A dermoscopy image of a single skin lesion: 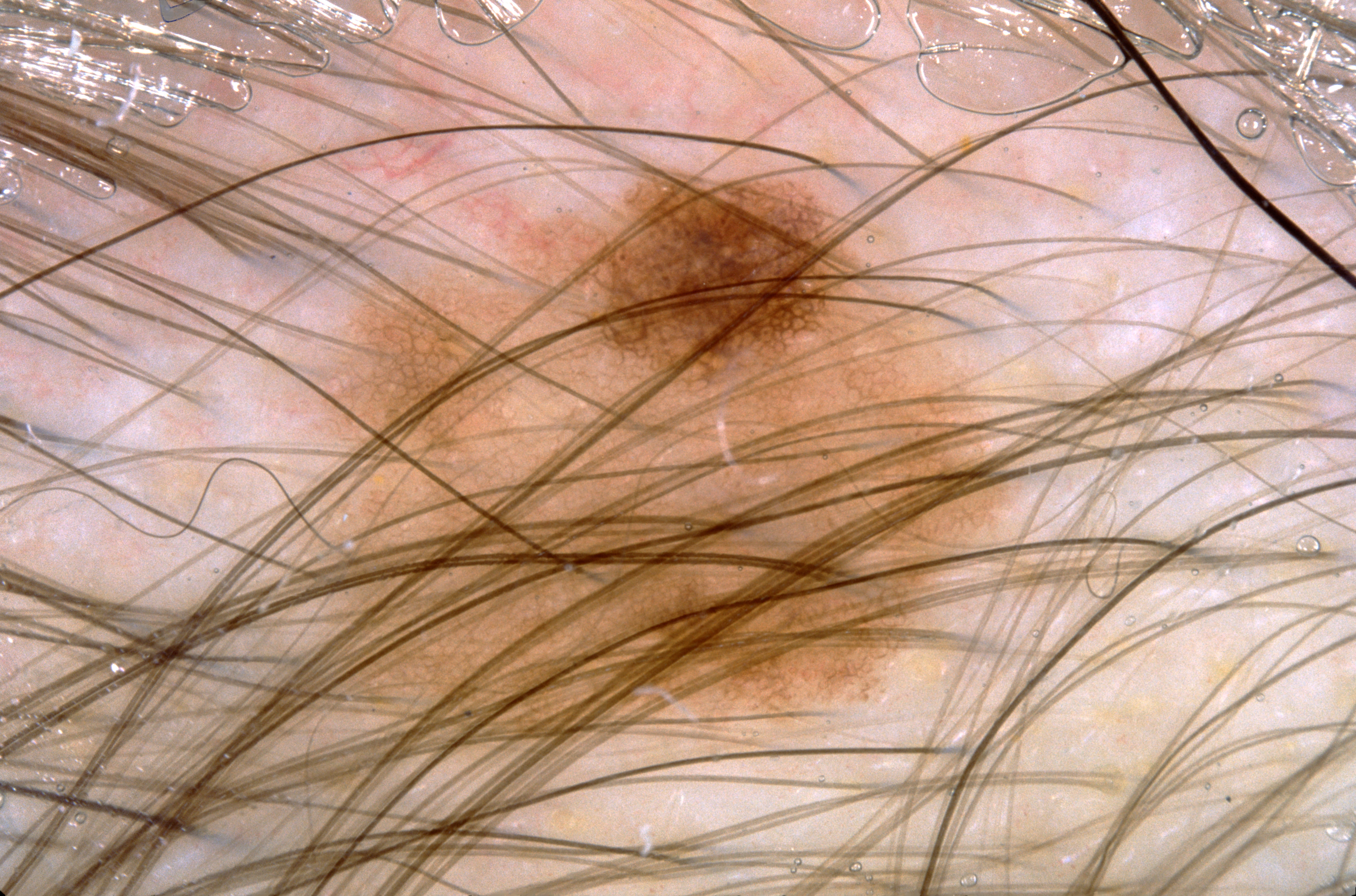Dermoscopic review identifies pigment network; no milia-like cysts, streaks, or negative network. The lesion spans x1=187, y1=163, x2=1042, y2=759. Clinically diagnosed as a melanocytic nevus.